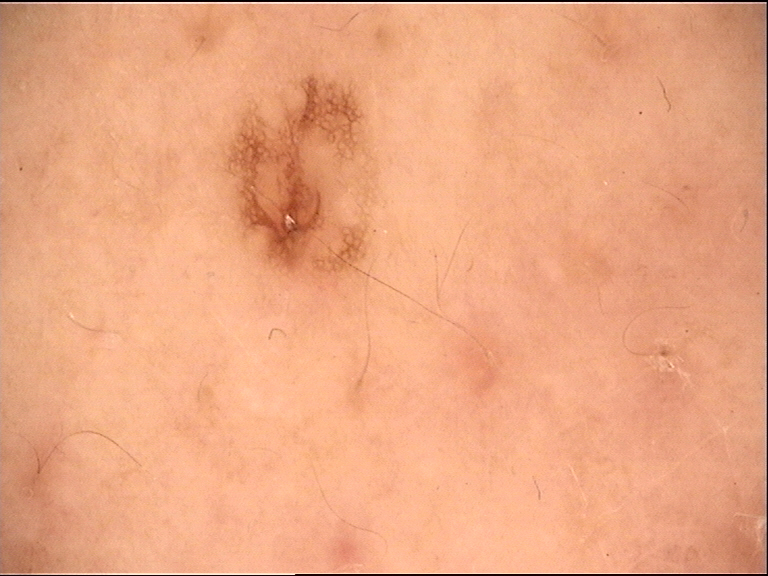Classified as a dysplastic junctional nevus.